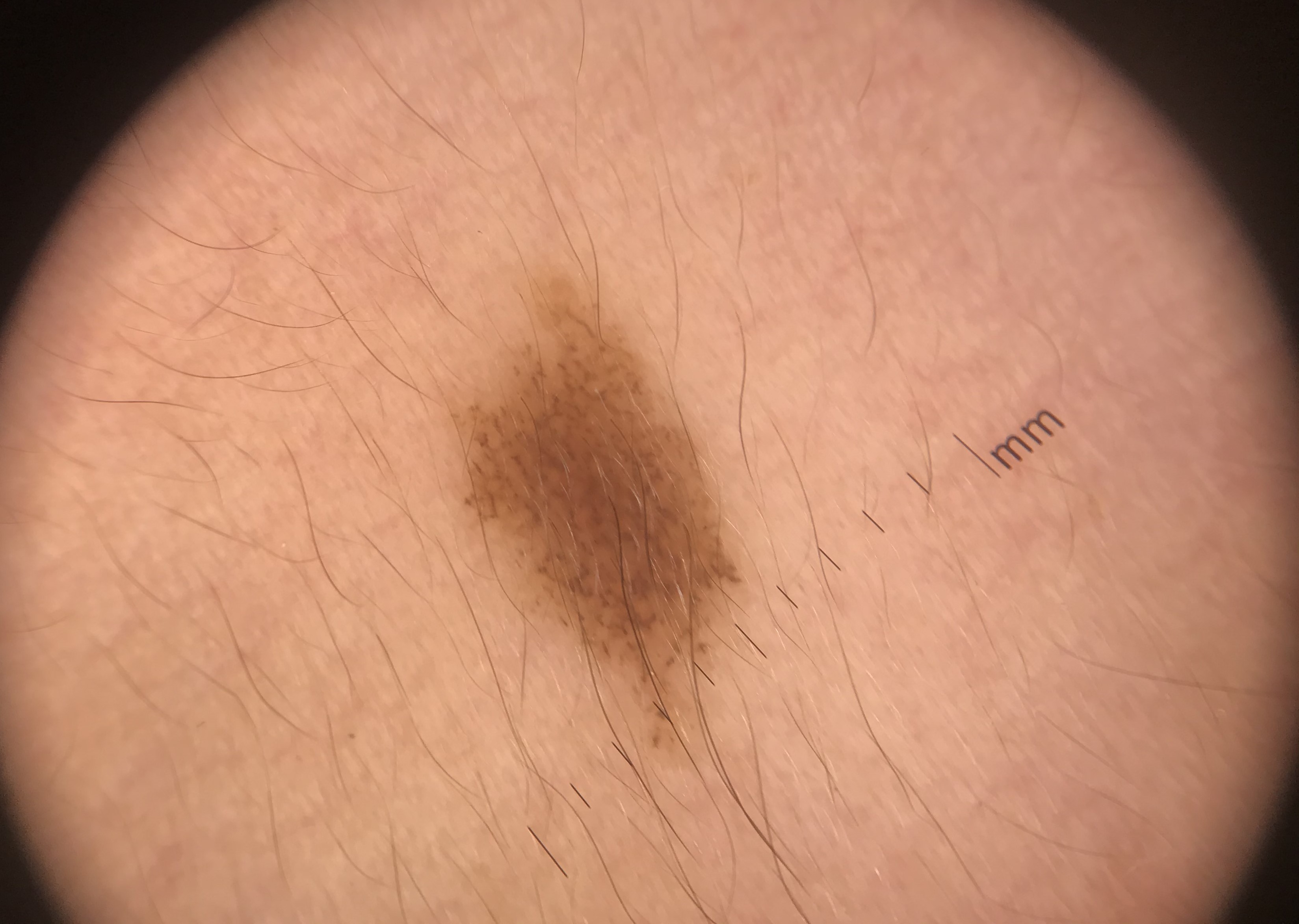{
  "diagnosis": {
    "name": "dysplastic junctional nevus",
    "code": "jd",
    "malignancy": "benign",
    "super_class": "melanocytic",
    "confirmation": "expert consensus"
  }
}